A dermoscopic photograph of a skin lesion.
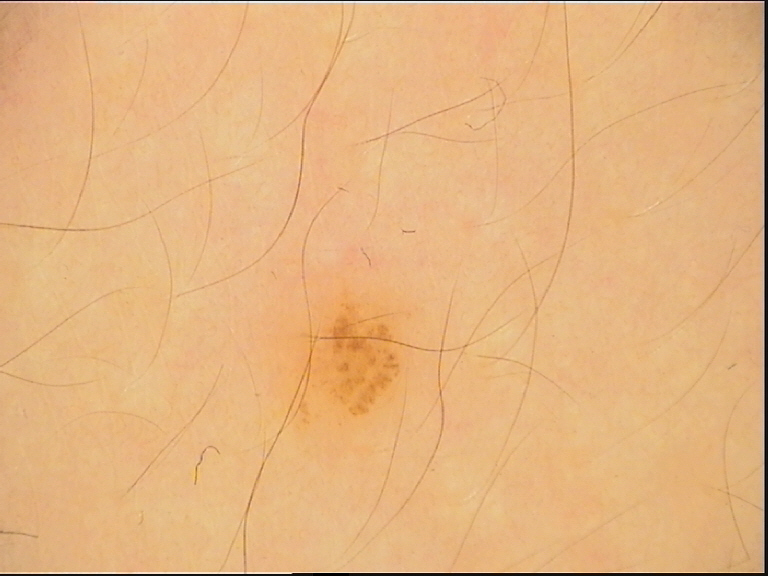assessment=dysplastic junctional nevus (expert consensus).